The photo was captured at a distance. The leg, back of the hand and arm are involved.
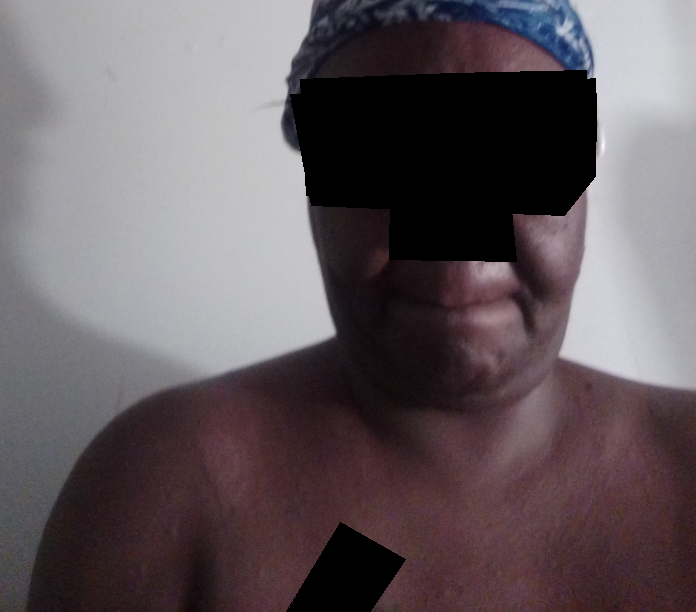Assessment: The skin condition could not be confidently assessed from this image.